Dermoscopy of a skin lesion: 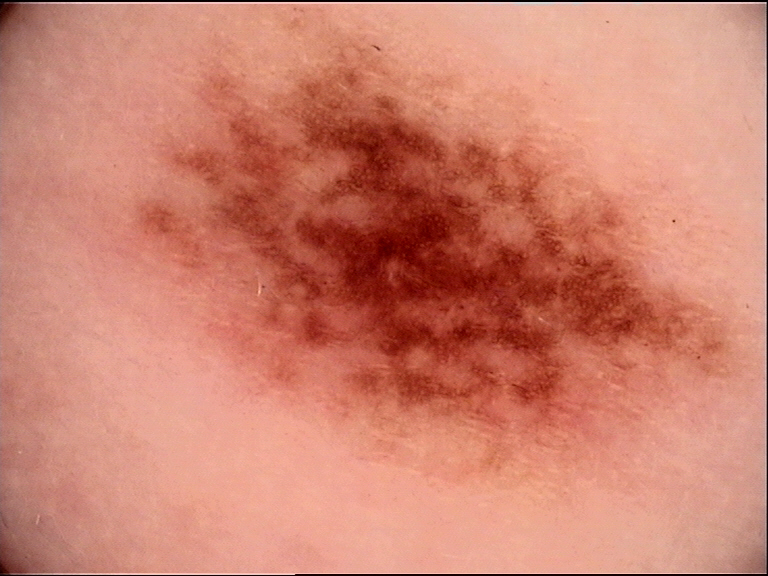Labeled as a benign lesion — a dysplastic junctional nevus.